Texture is reported as fluid-filled and raised or bumpy. The condition has been present for one to four weeks. The lesion is associated with enlargement and itching. The arm is involved. Self-categorized by the patient as a rash. An image taken at an angle: 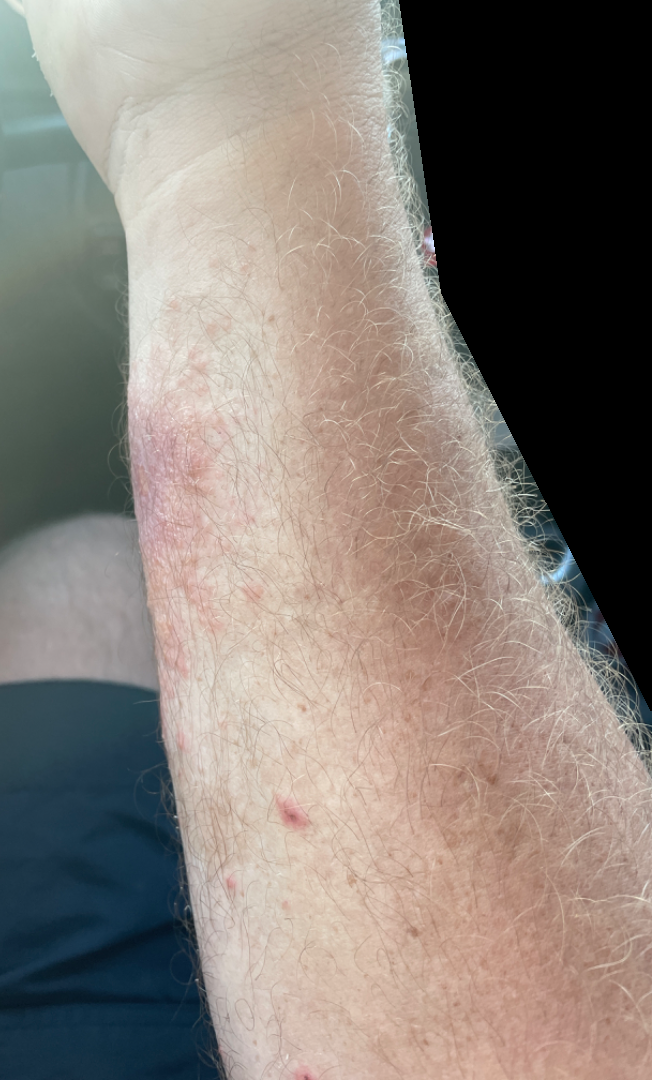<dermatology_case>
<differential>
  <leading>Allergic Contact Dermatitis</leading>
</differential>
</dermatology_case>